Skin tone: Fitzpatrick skin type IV · this image was taken at an angle.
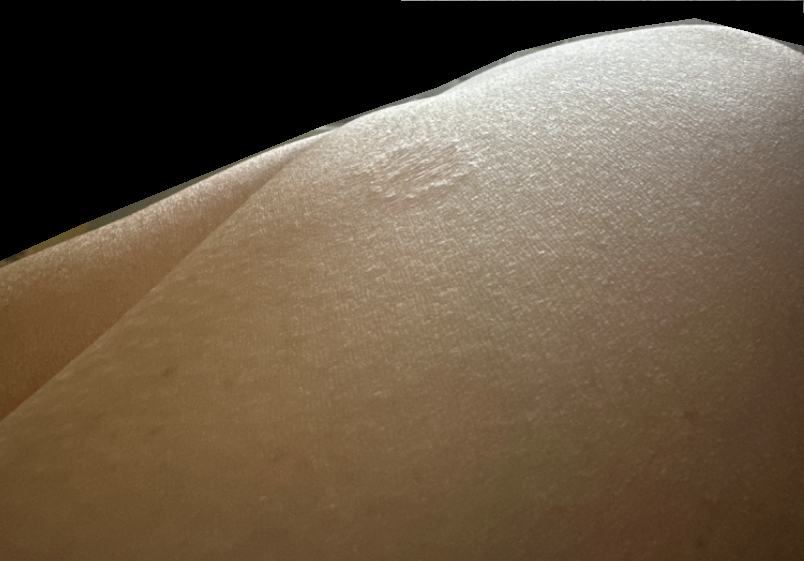On remote review of the image: Tinea, Eczema and Psoriasis were each considered, in no particular order.